A dermoscopic photograph of a skin lesion: 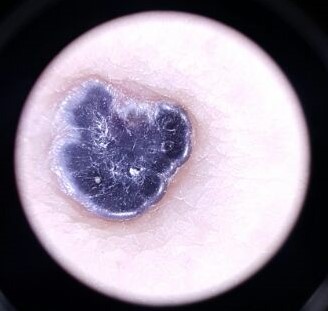The architecture is that of a vascular lesion.
Consistent with a benign lesion — an angiokeratoma.